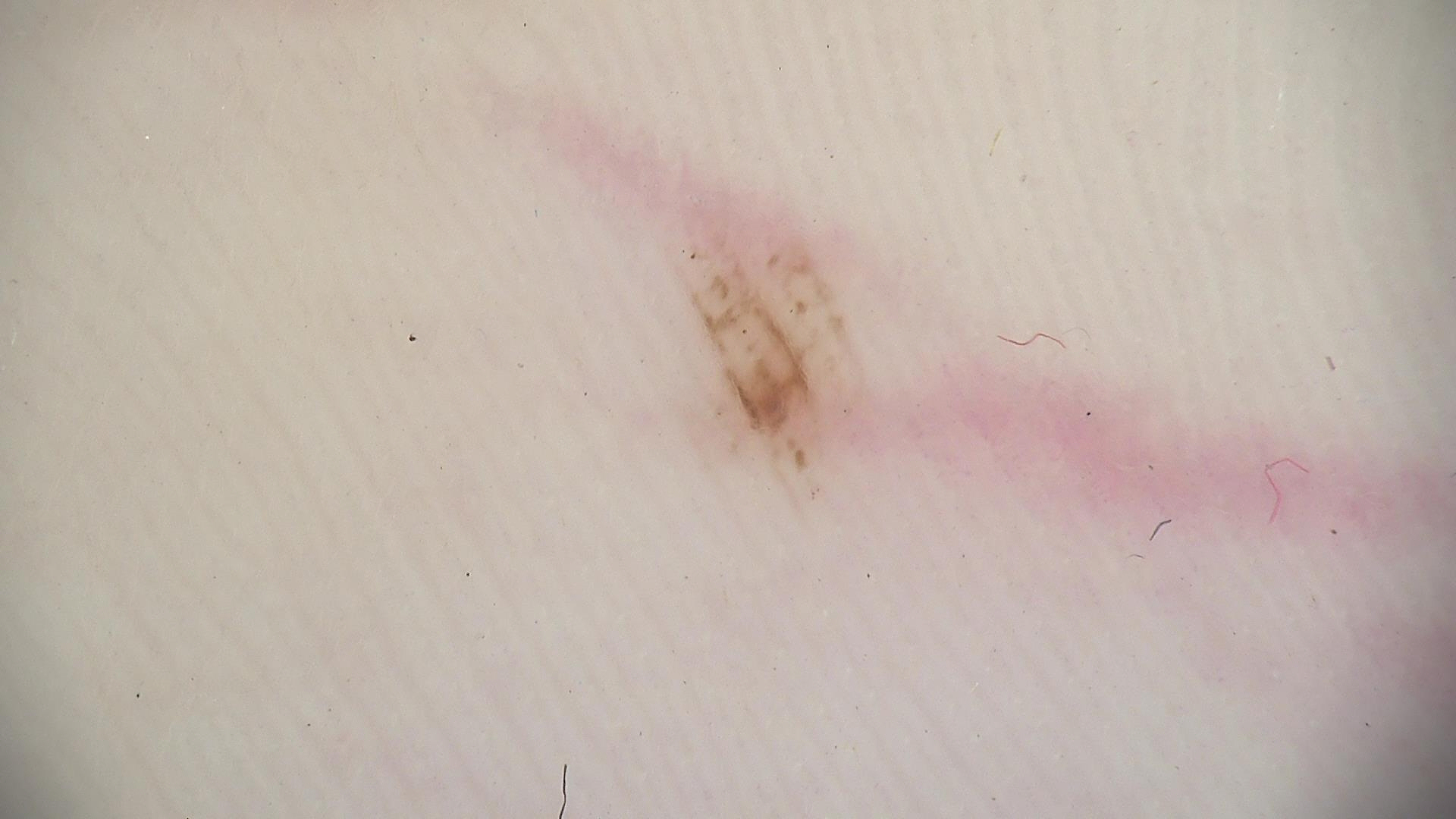Labeled as an acral dysplastic junctional nevus.